An image taken at an angle; the front of the torso is involved: 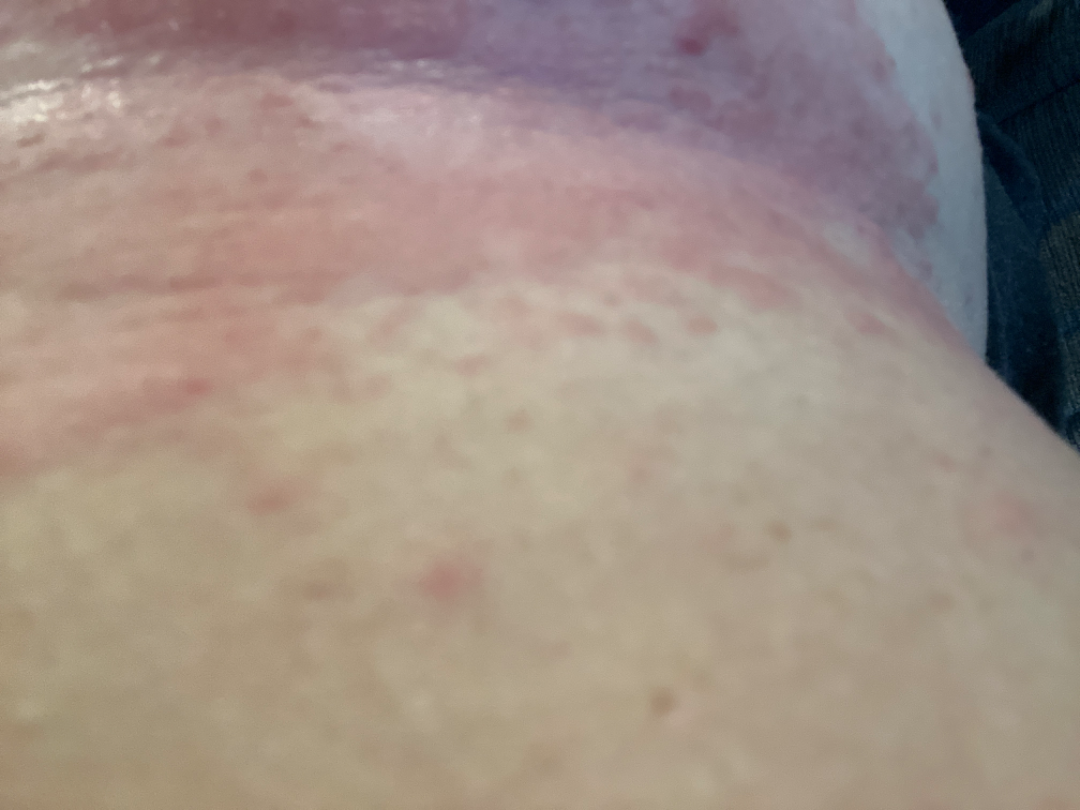One reviewing dermatologist: most consistent with Candida intertrigo; also raised was Allergic Contact Dermatitis; a more distant consideration is Psoriasis.